A dermoscopic photograph of a skin lesion:
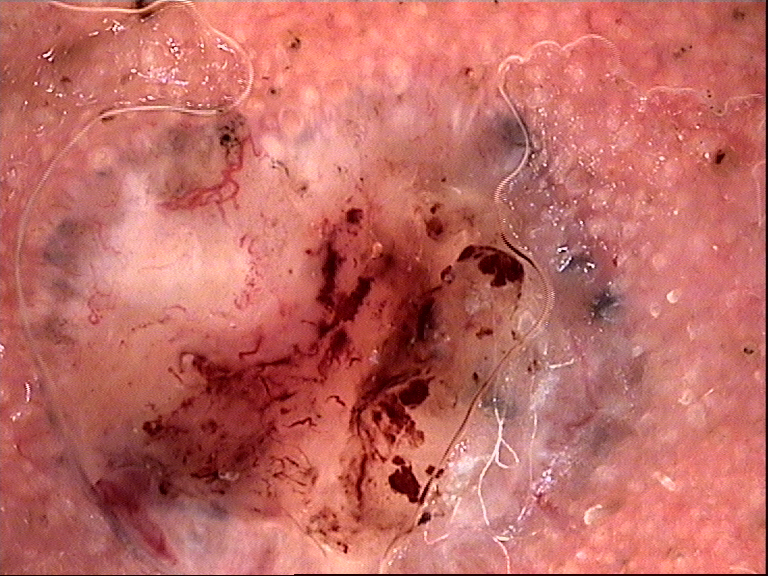The architecture is that of a keratinocytic lesion. Confirmed on histopathology as a malignancy — a basal cell carcinoma.